The lesion is described as raised or bumpy, rough or flaky and fluid-filled · located on the leg and arm · the patient also reports fatigue · male subject, age 40–49 · close-up view: 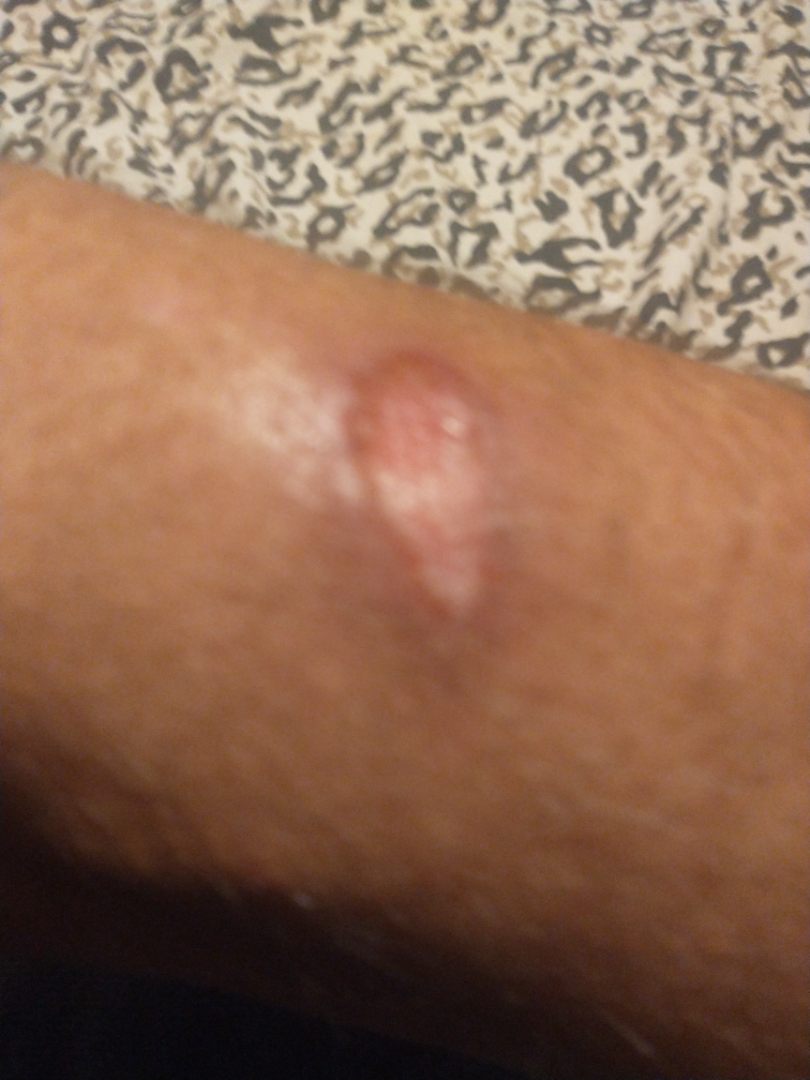The reviewing panel's impression was: consistent with Scar Condition.